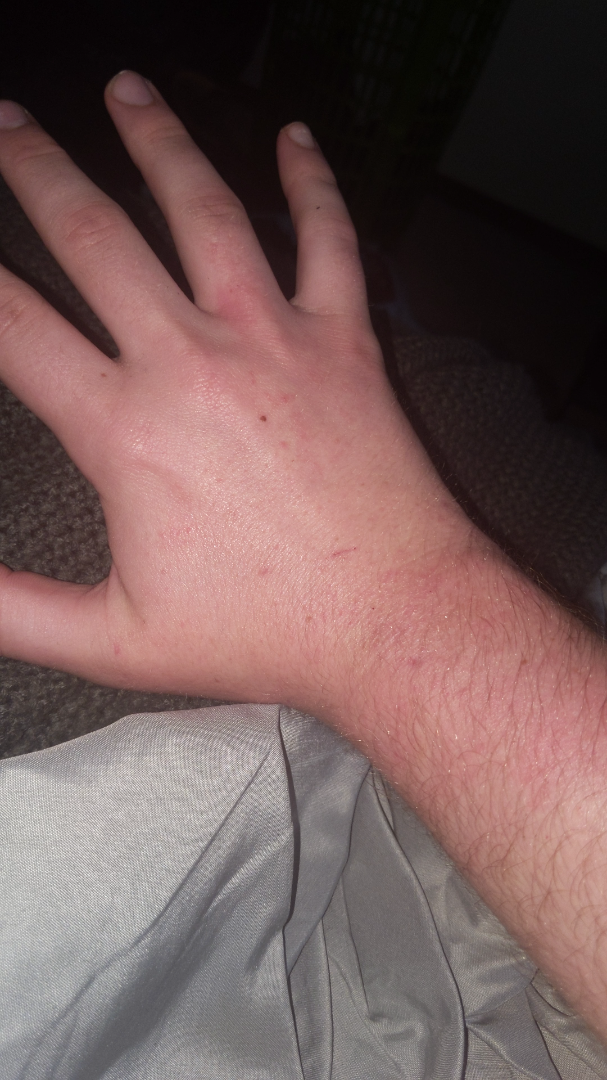This is a close-up image.
The reviewing clinician's impression was: in keeping with Allergic Contact Dermatitis.